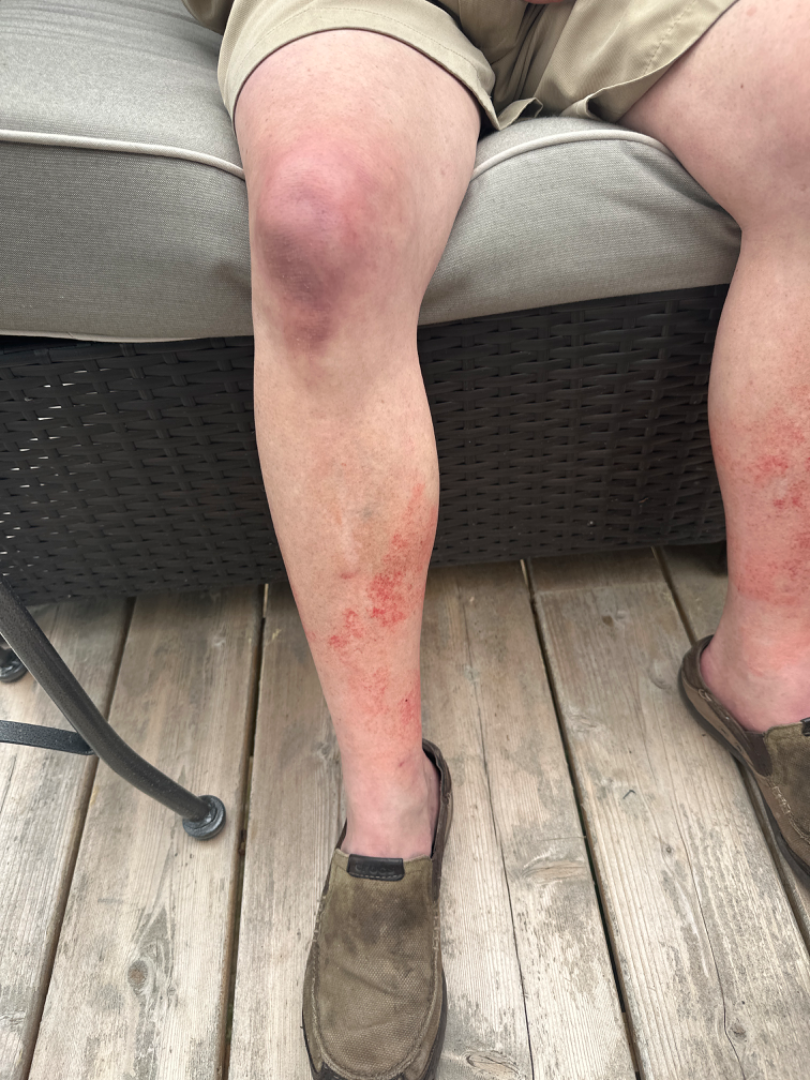Texture is reported as flat. The condition has been present for less than one week. This image was taken at a distance. The affected area is the leg. No associated lesion symptoms were reported. On teledermatology review, most likely Pigmented purpuric eruption.